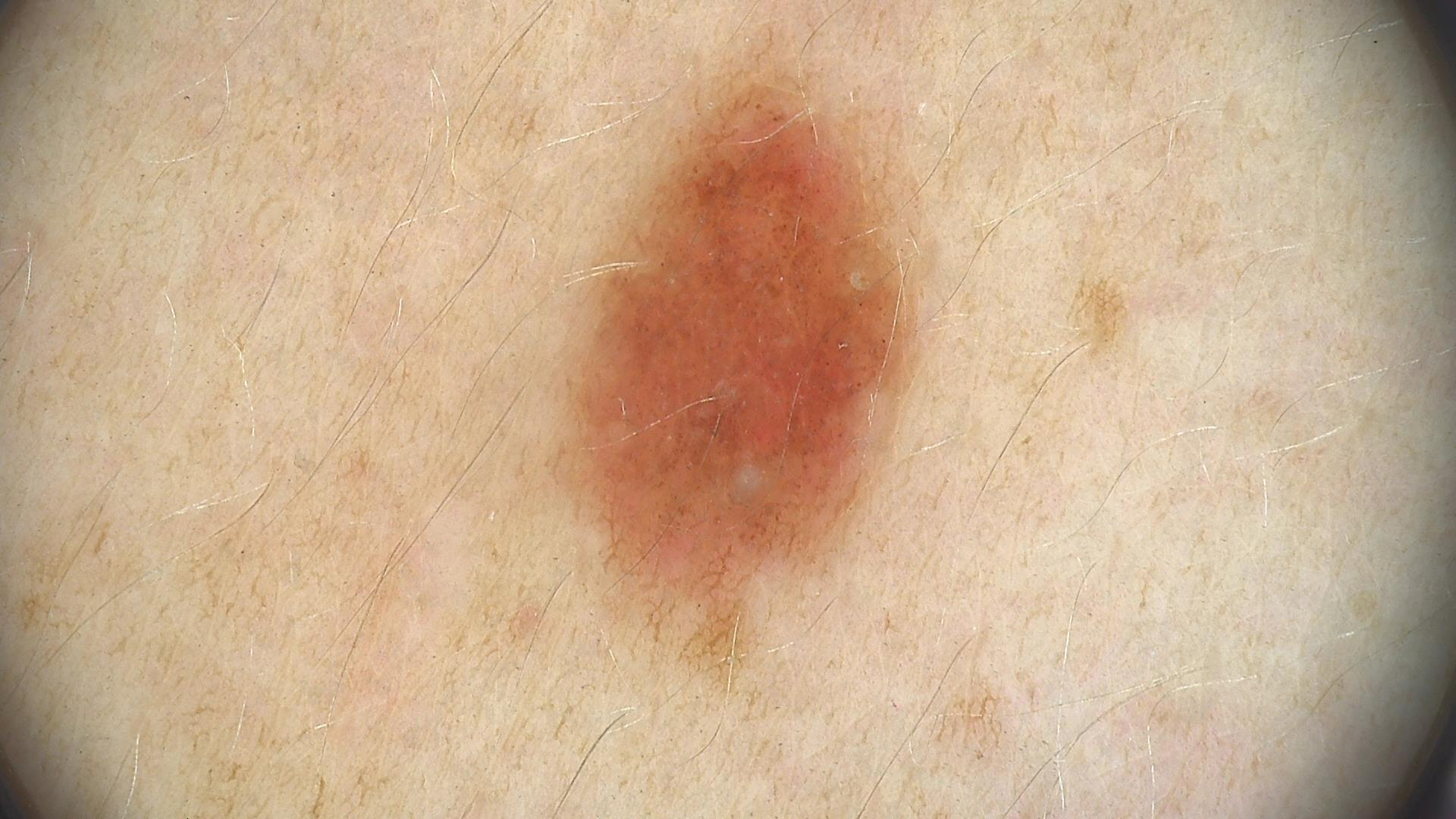Q: What kind of image is this?
A: dermoscopy
Q: What is the diagnosis?
A: dysplastic junctional nevus (expert consensus)